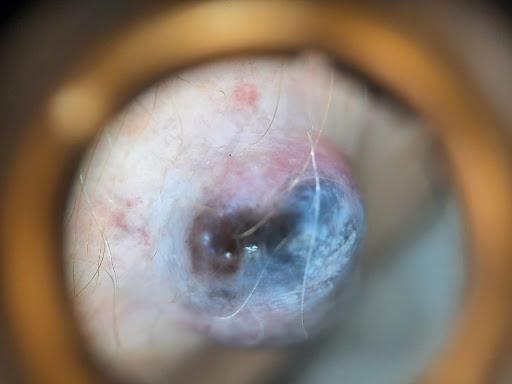• skin phototype — I
• modality — contact-polarized dermoscopy
• subject — male, in their mid- to late 80s or older
• anatomic site — an upper extremity
• pathology — Melanoma (biopsy-proven)